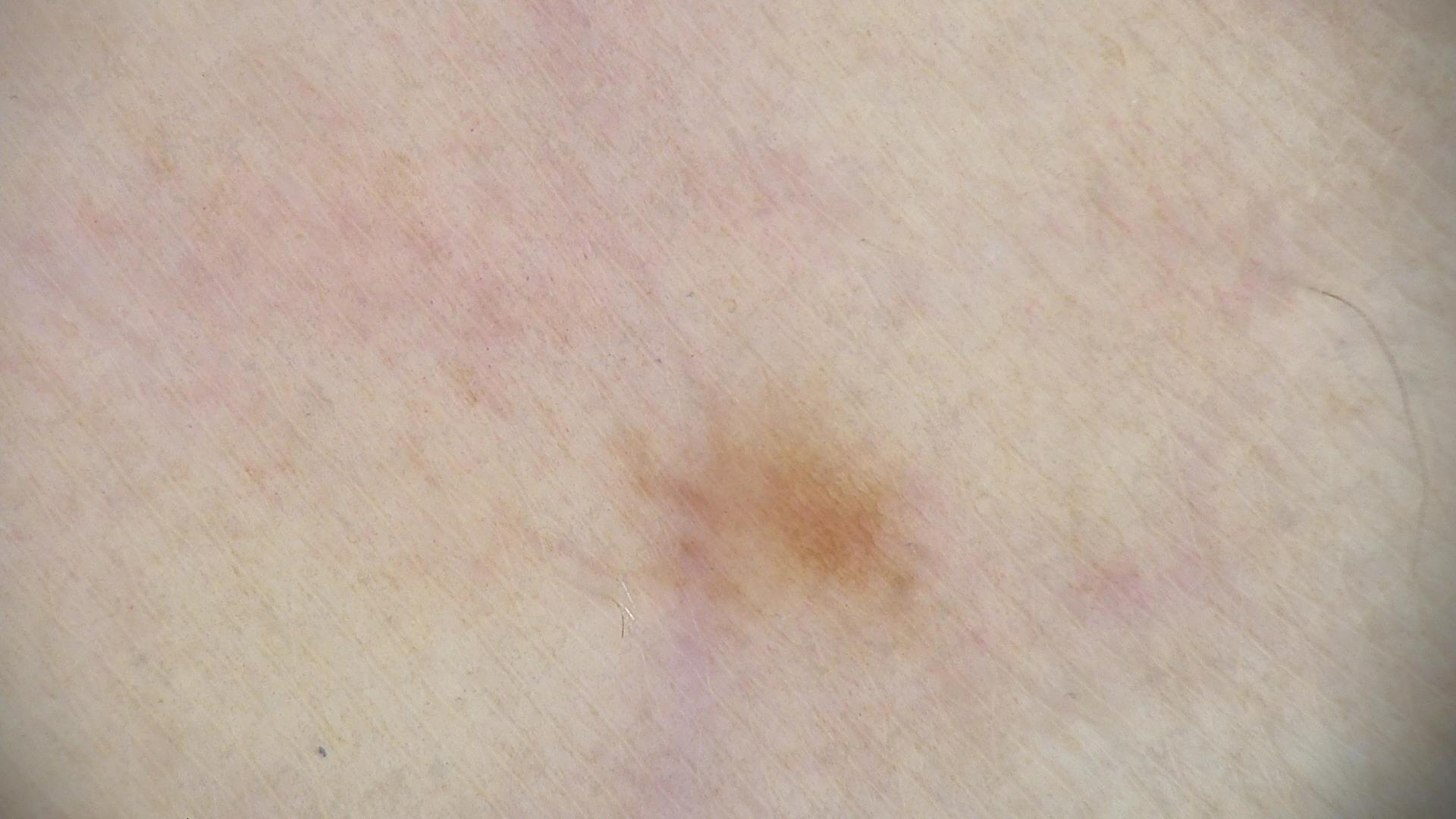* category · banal
* class · junctional nevus (expert consensus)